The affected area is the back of the hand · skin tone: Fitzpatrick phototype IV · male patient, age 50–59 · the contributor reports the lesion is raised or bumpy · self-categorized by the patient as a rash · the photo was captured at an angle · the contributor reports the condition has been present for one to four weeks · the contributor reports itching:
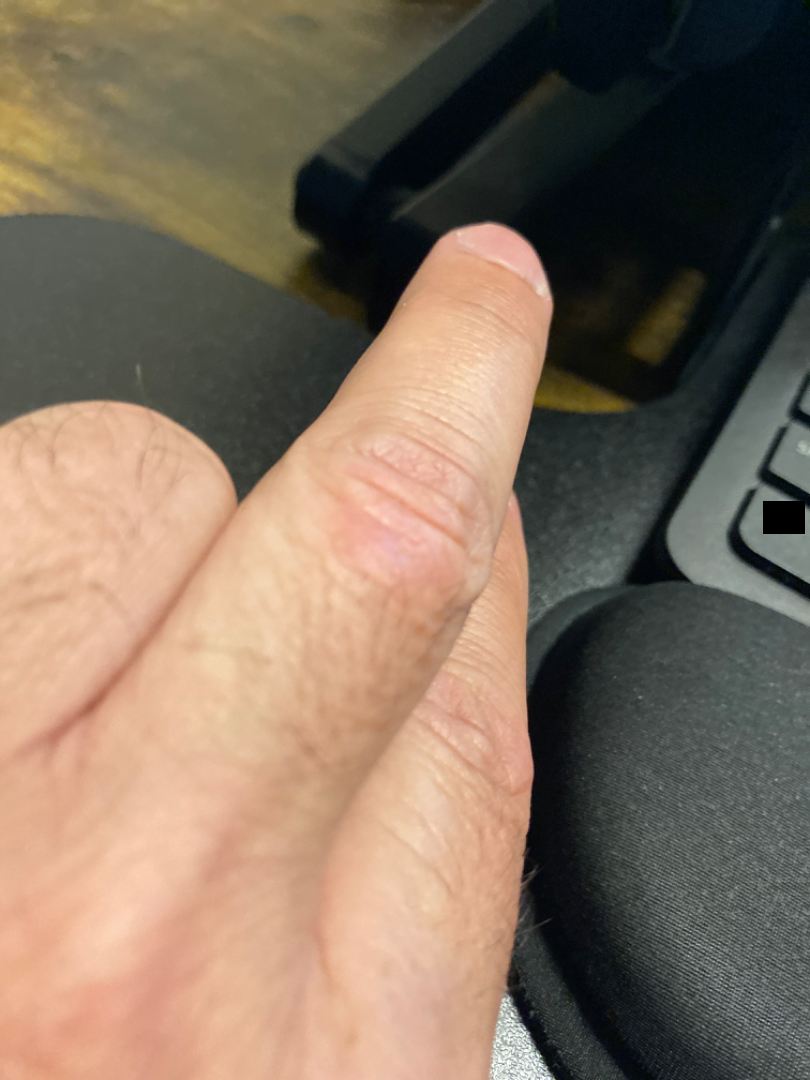Notes:
- assessment: unable to determine